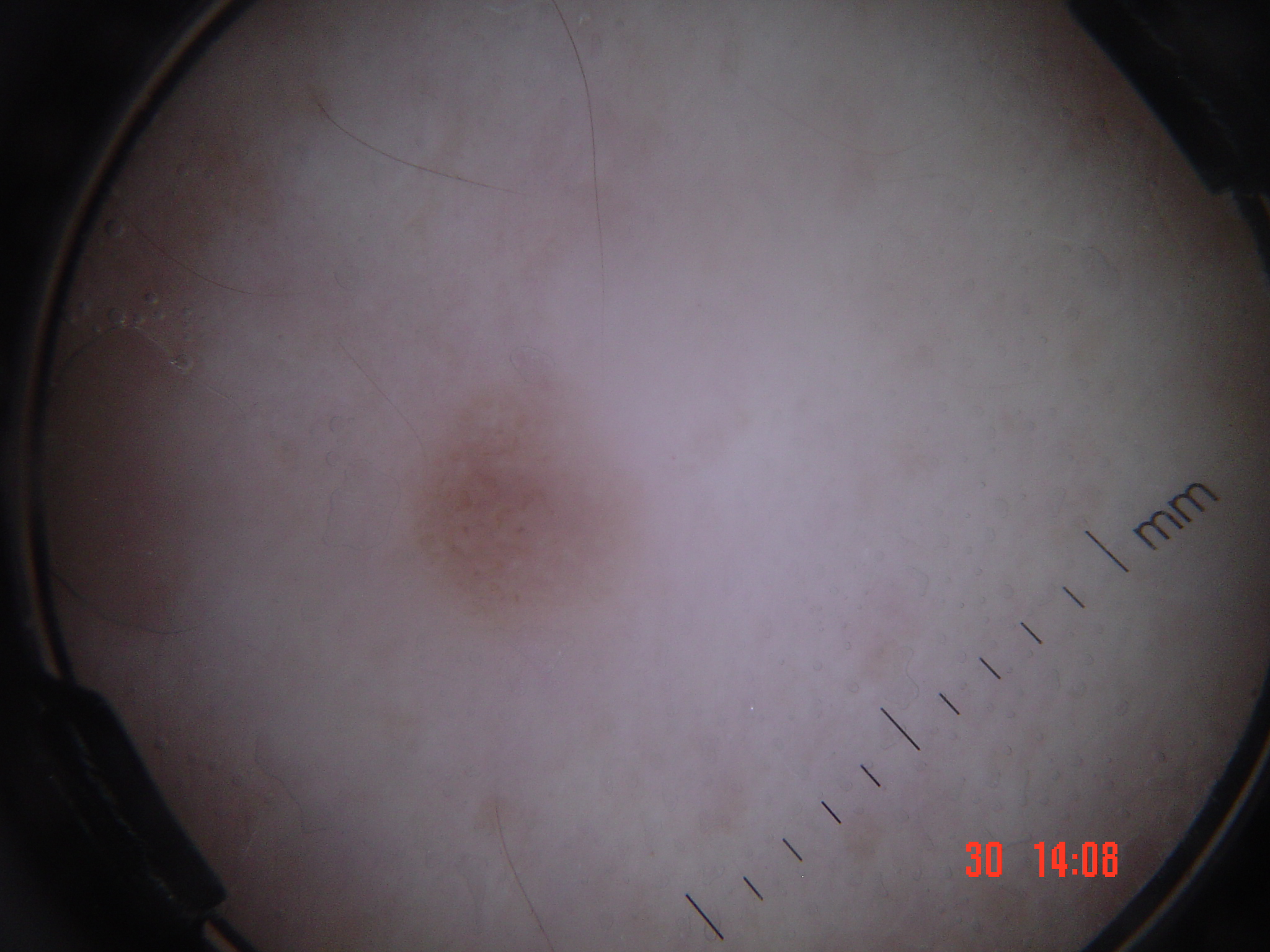imaging = dermatoscopy | diagnostic label = seborrheic keratosis (expert consensus).